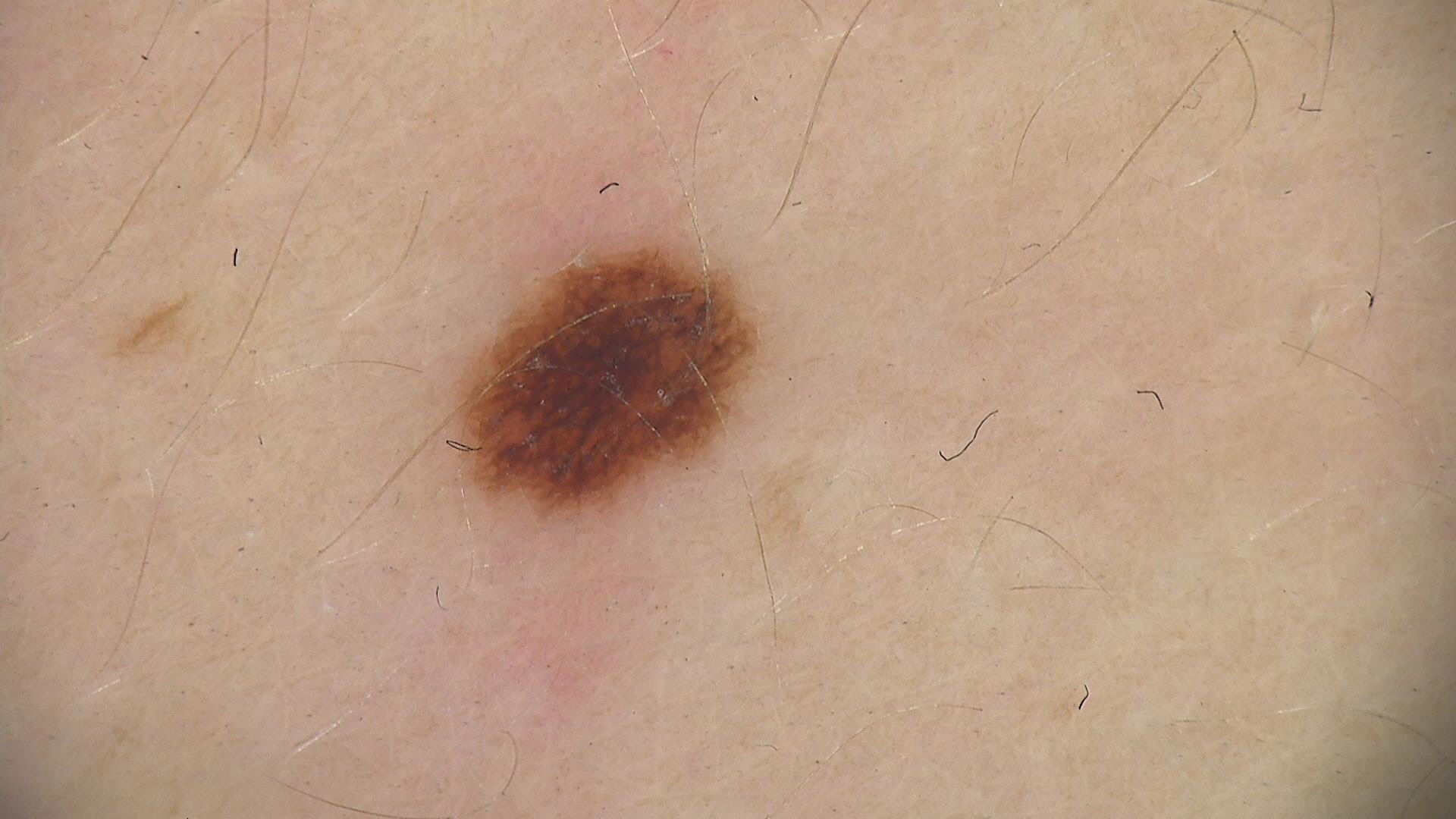assessment: dysplastic junctional nevus (expert consensus).